A dermoscopy image of a single skin lesion.
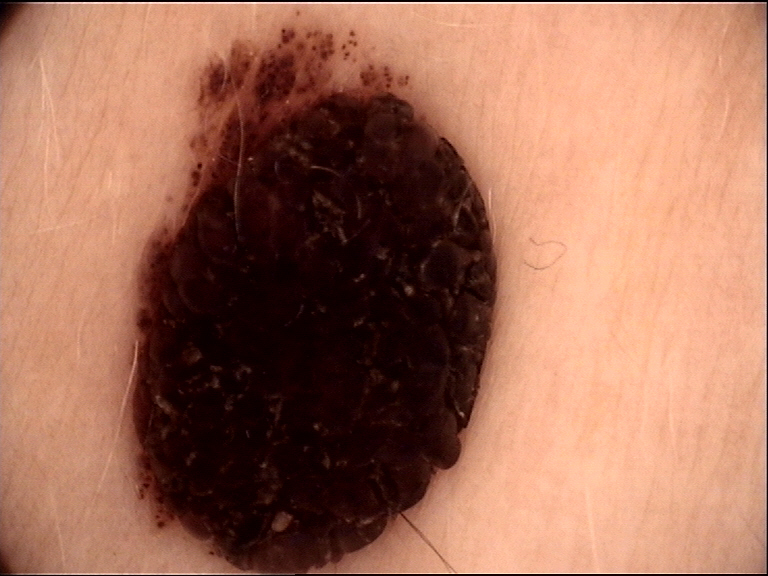Conclusion:
The diagnostic label was a banal lesion — a dermal nevus.